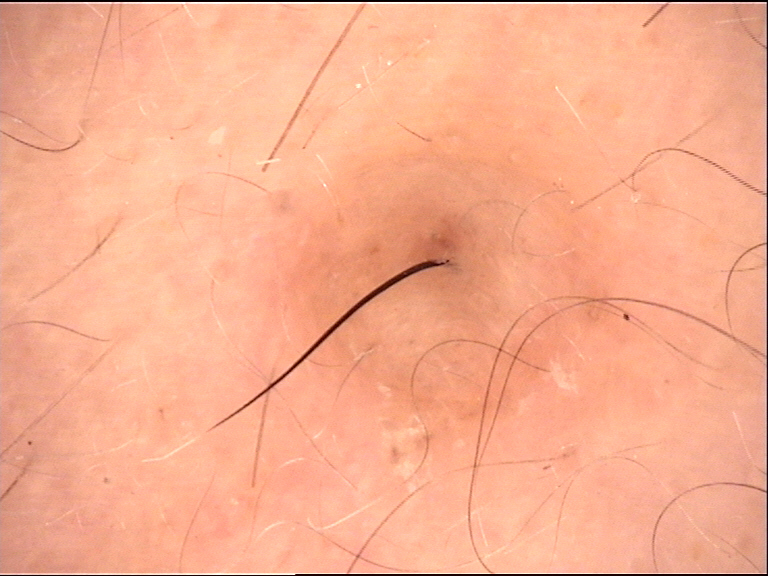label: dermal nevus (expert consensus).